A skin lesion imaged with a dermatoscope.
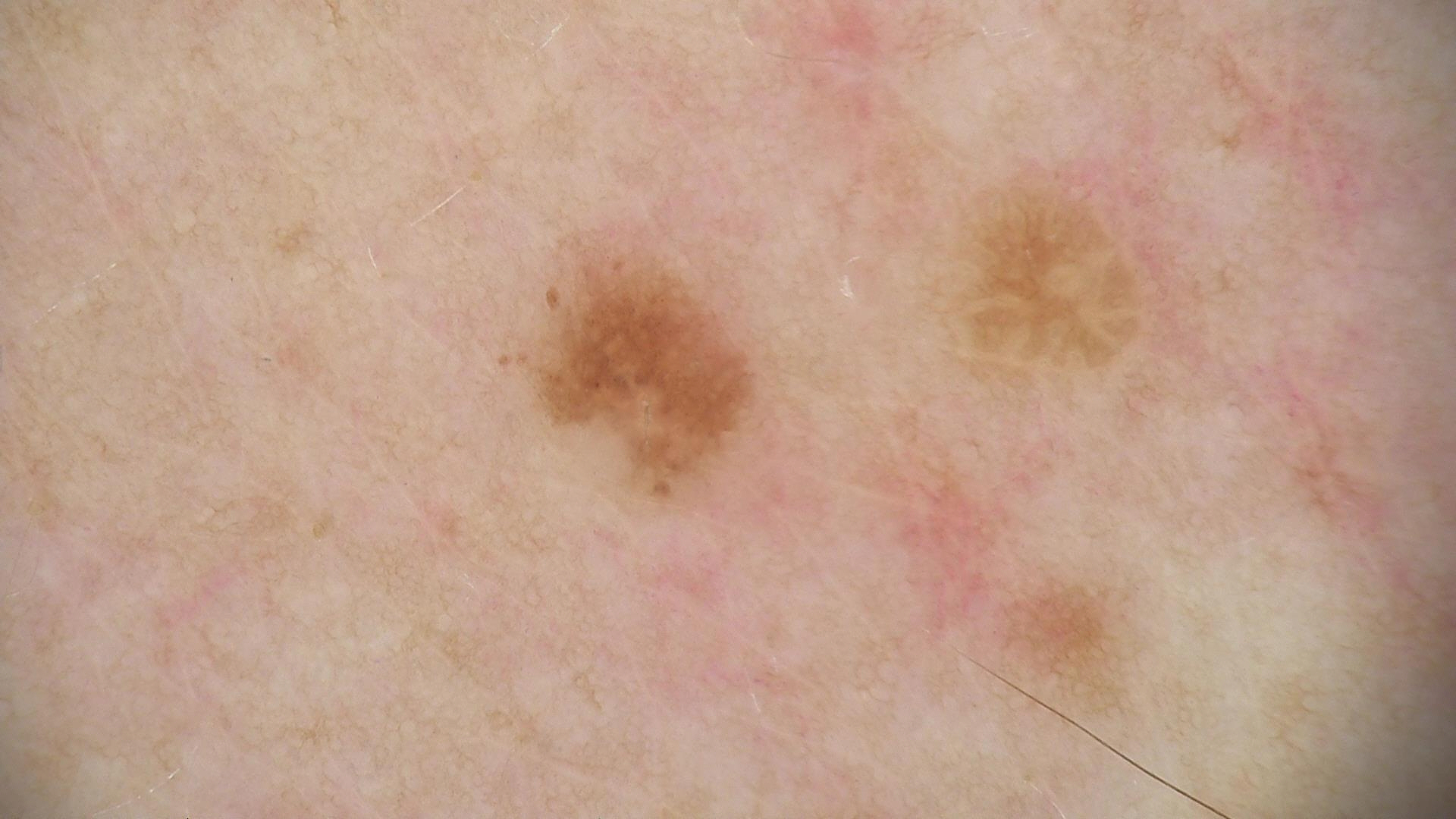label = dysplastic junctional nevus (expert consensus).